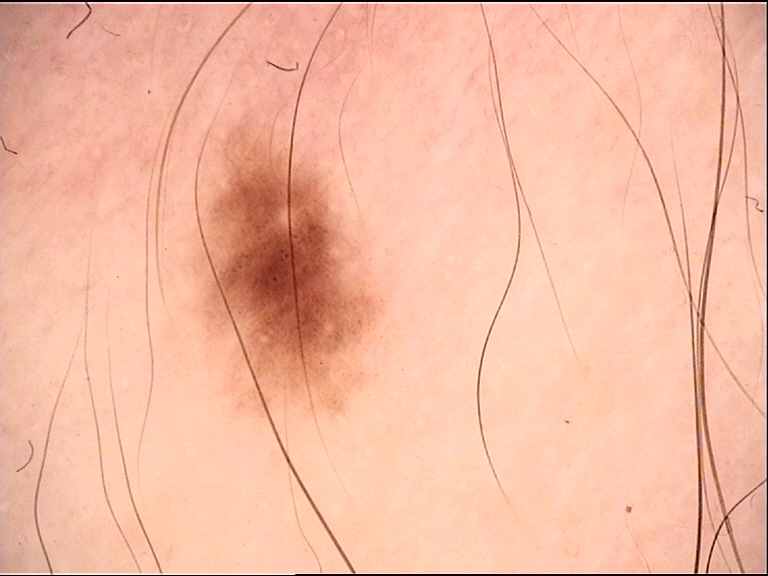A dermatoscopic image of a skin lesion. Consistent with a banal lesion — a junctional nevus.